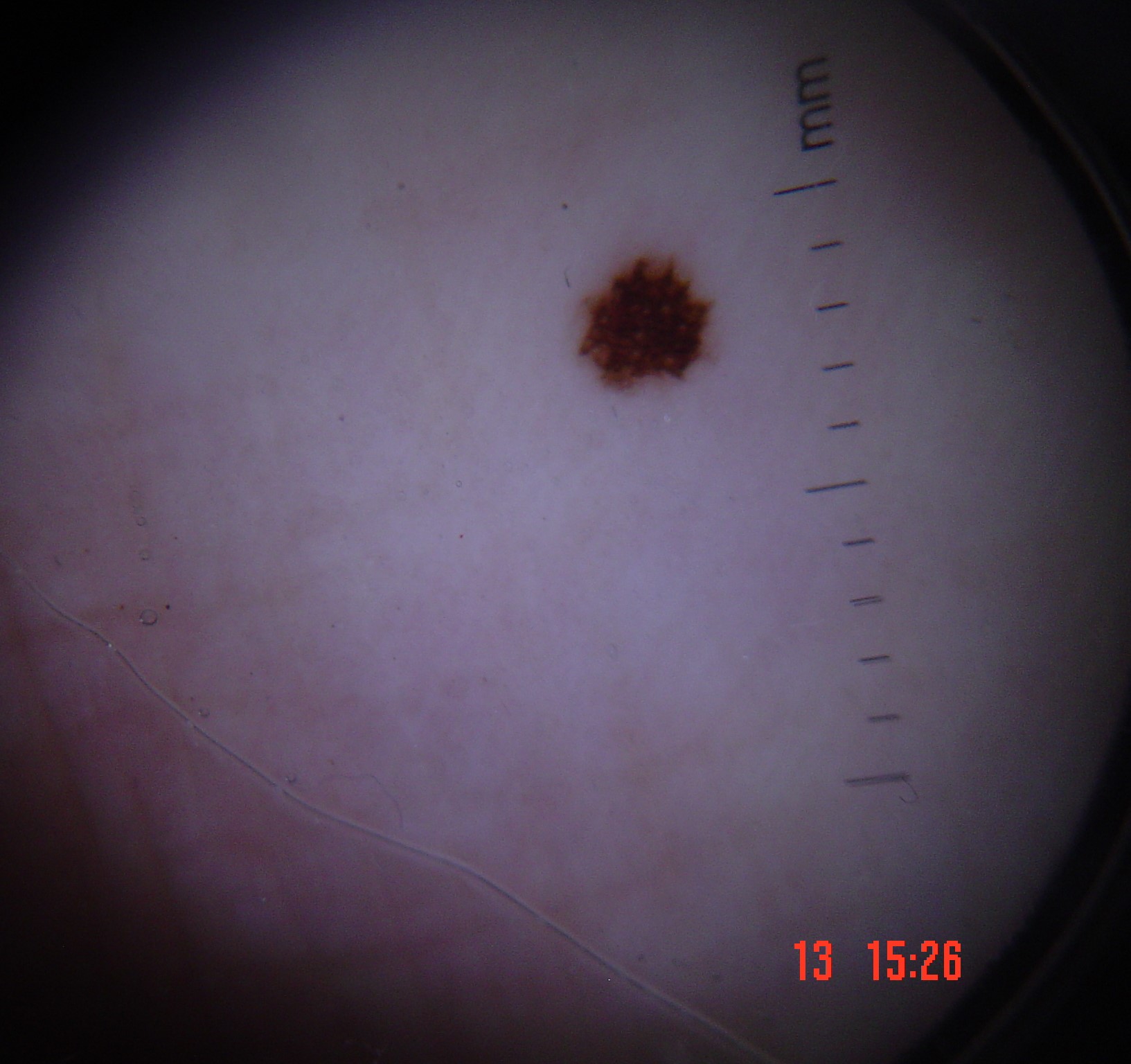Consistent with an acral dysplastic junctional nevus.